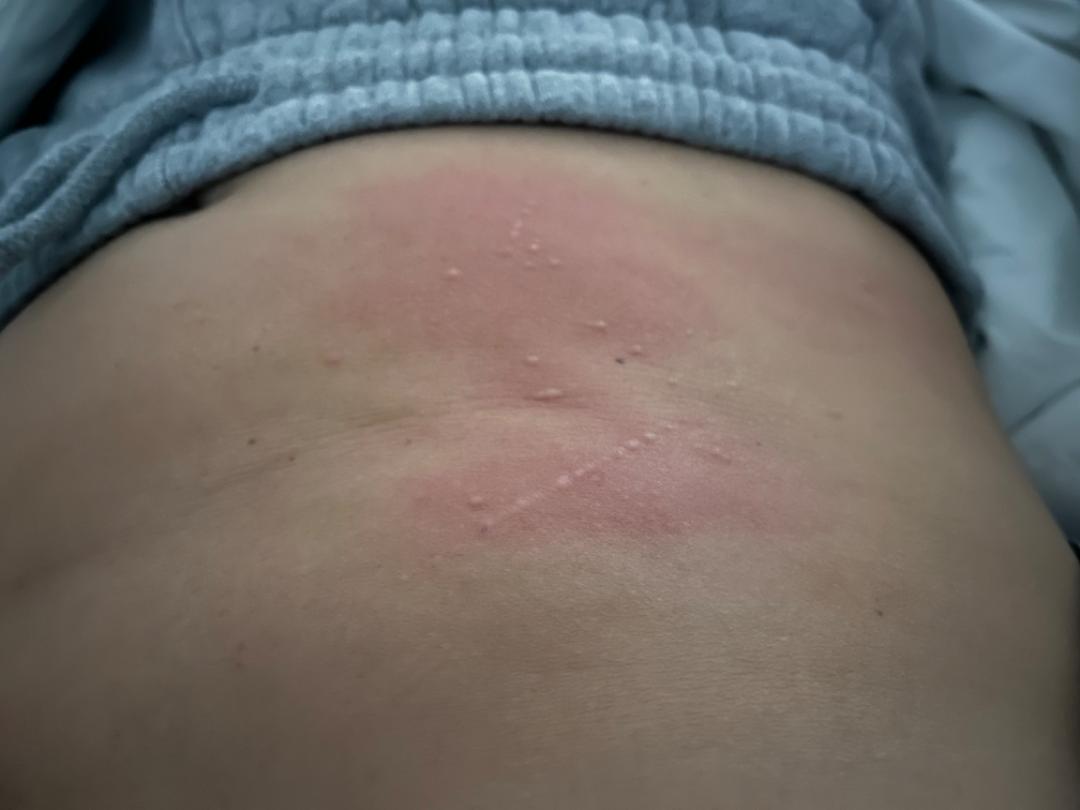Q: Age and sex?
A: female, age 30–39
Q: Where on the body?
A: arm, front of the torso and back of the torso
Q: What is the framing?
A: close-up
Q: What is the differential diagnosis?
A: Lichen striatus (possible); Acute dermatitis, NOS (possible)